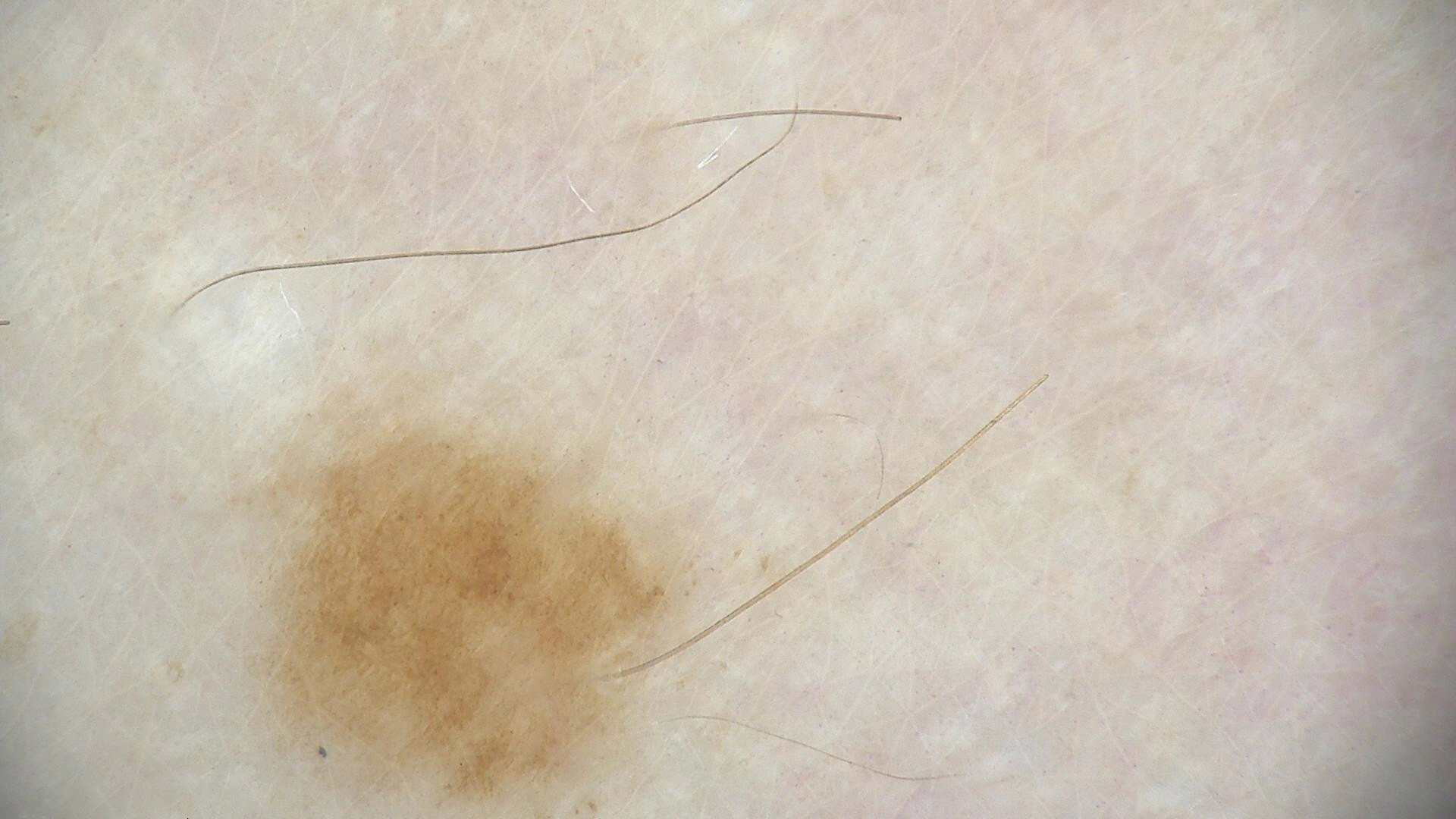image type: dermoscopy; diagnostic label: dysplastic junctional nevus (expert consensus).